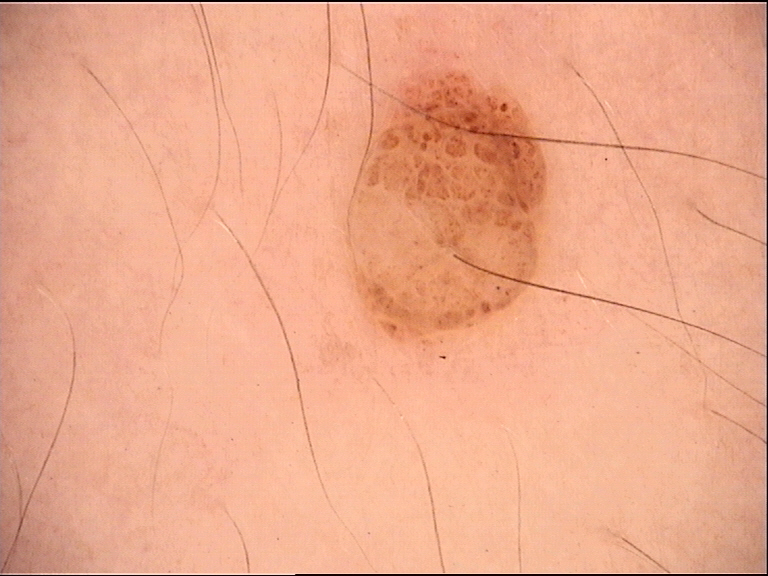{"lesion_type": {"main_class": "banal", "pattern": "dermal"}, "diagnosis": {"name": "dermal nevus", "code": "db", "malignancy": "benign", "super_class": "melanocytic", "confirmation": "expert consensus"}}